A dermoscopy image of a single skin lesion.
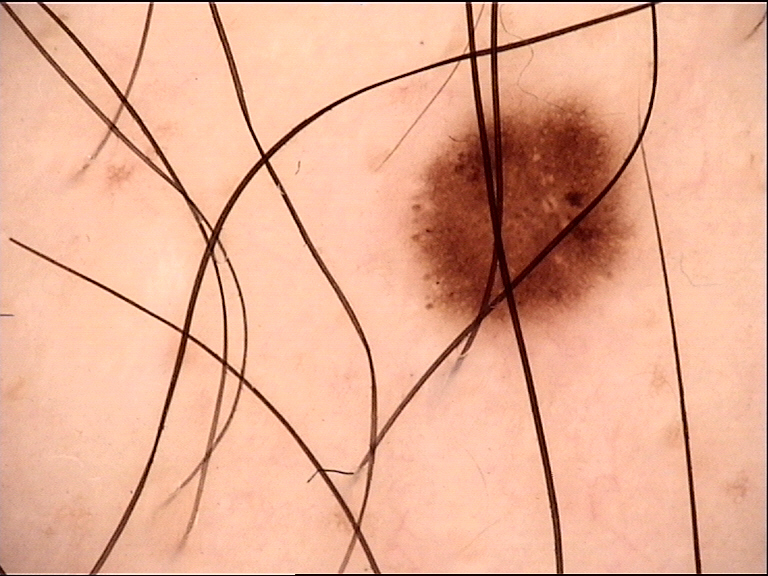Impression:
Classified as a dysplastic junctional nevus.